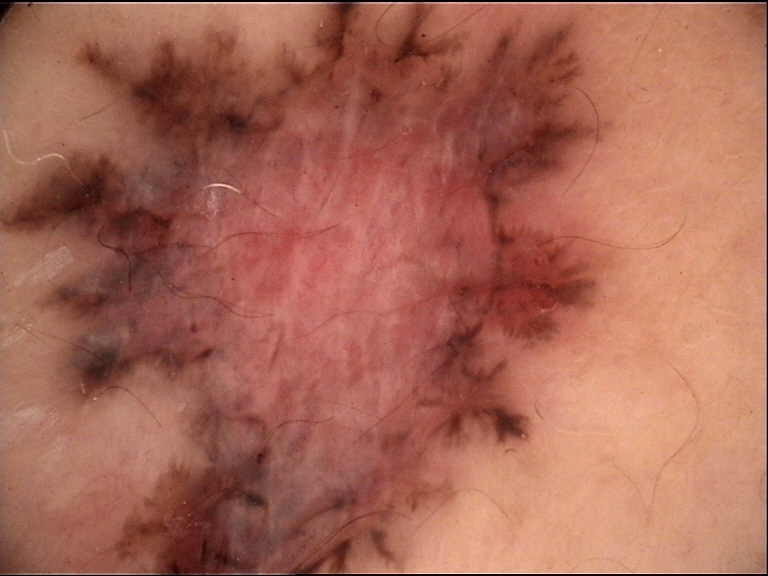  image: dermoscopy
  lesion_type:
    main_class: keratinocytic
  diagnosis:
    name: basal cell carcinoma
    code: bcc
    malignancy: malignant
    super_class: non-melanocytic
    confirmation: histopathology